Present for less than one week; a close-up photograph; located on the head or neck: 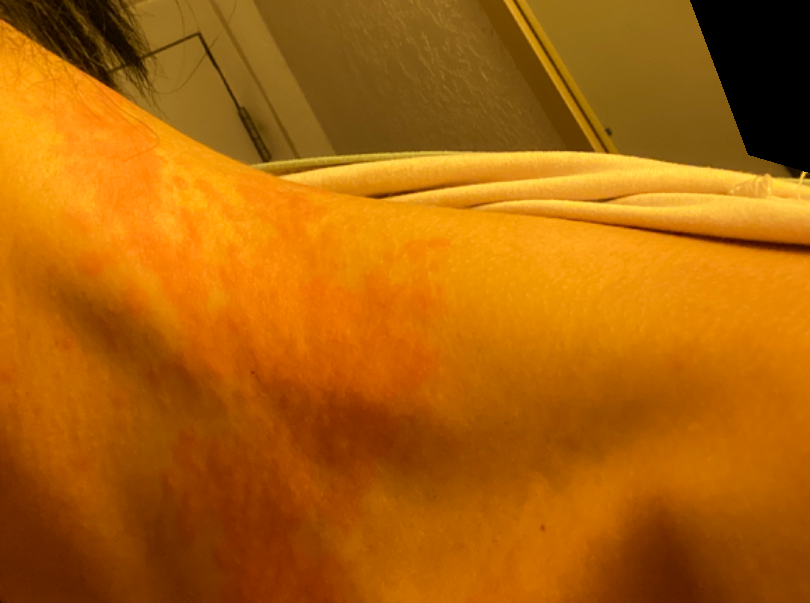Impression: The case was indeterminate on photographic review.